The back of the torso is involved. The lesion is described as fluid-filled and raised or bumpy. The patient considered this a rash. This is a close-up image. The patient also reports shortness of breath and fatigue. Symptoms reported: enlargement and itching. Present for less than one week. Skin tone: FST III:
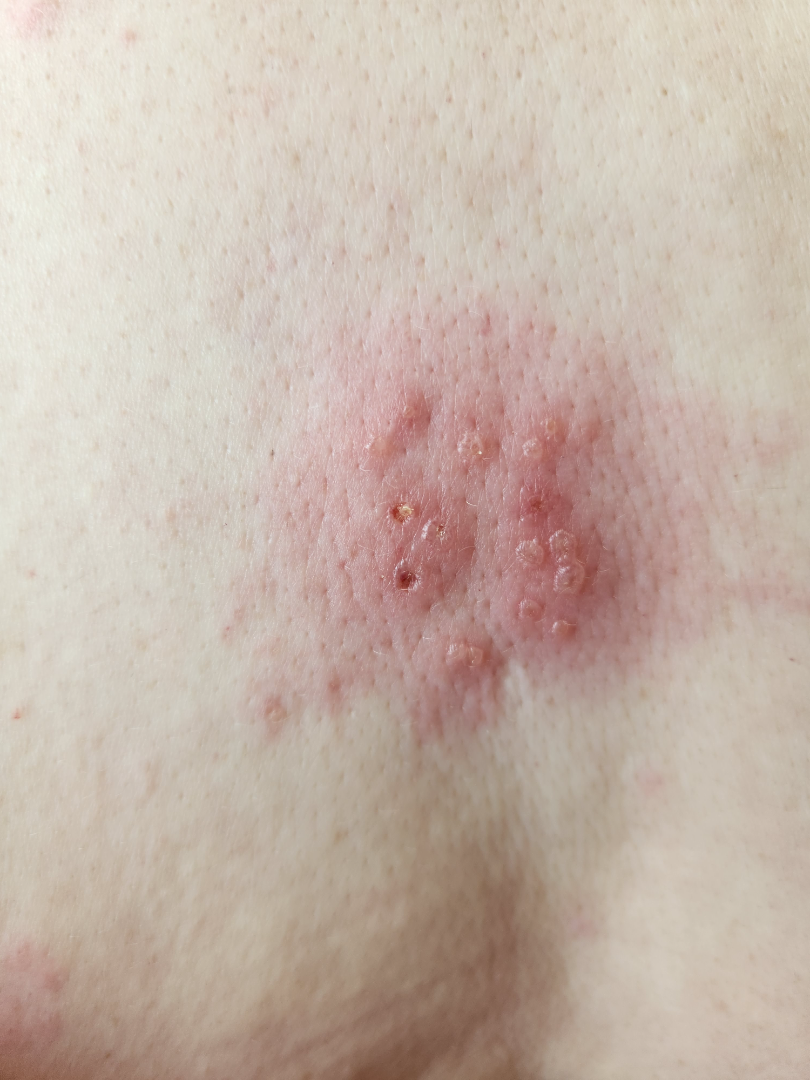Review:
A single dermatologist reviewed the case: the favored diagnosis is Herpes Simplex; also consider Herpes Zoster.